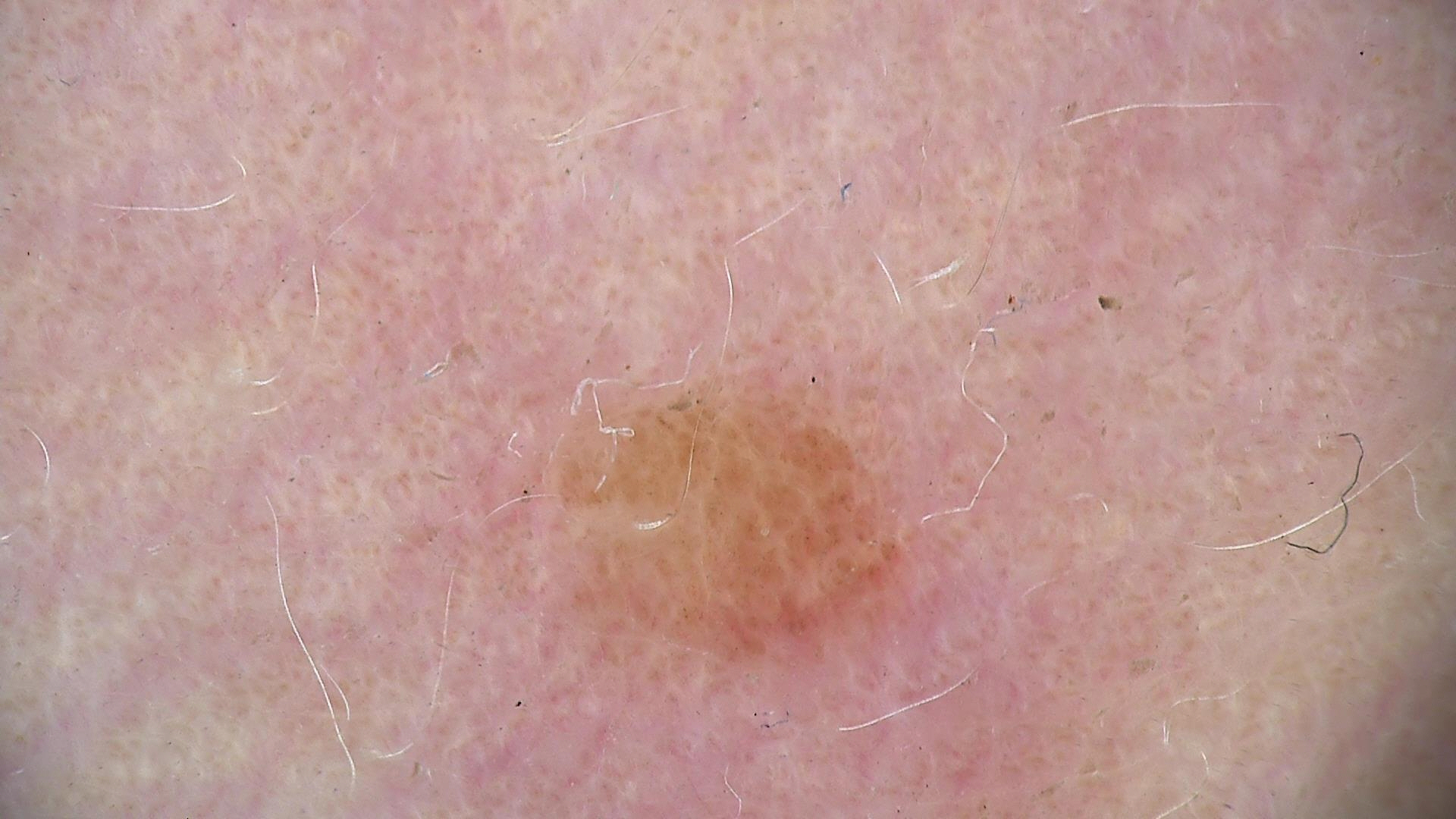diagnostic label = dysplastic junctional nevus (expert consensus).